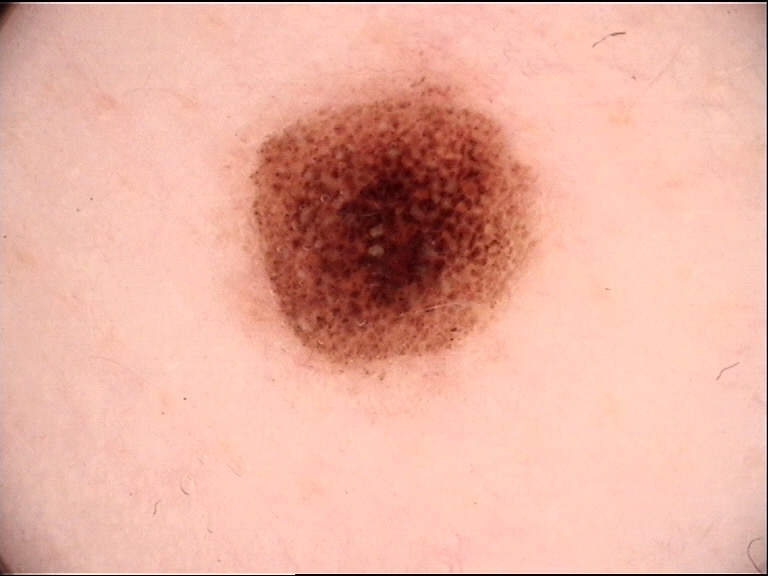lesion type: banal, assessment: compound nevus (expert consensus).